A dermoscopic close-up of a skin lesion.
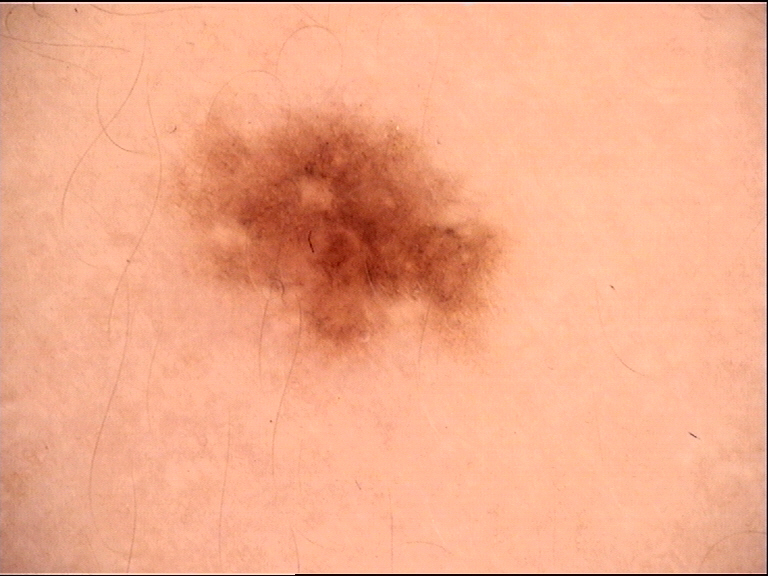<dermoscopy>
  <diagnosis>
    <name>dysplastic junctional nevus</name>
    <code>jd</code>
    <malignancy>benign</malignancy>
    <super_class>melanocytic</super_class>
    <confirmation>expert consensus</confirmation>
  </diagnosis>
</dermoscopy>